This image was taken at an angle. Skin tone: FST V — 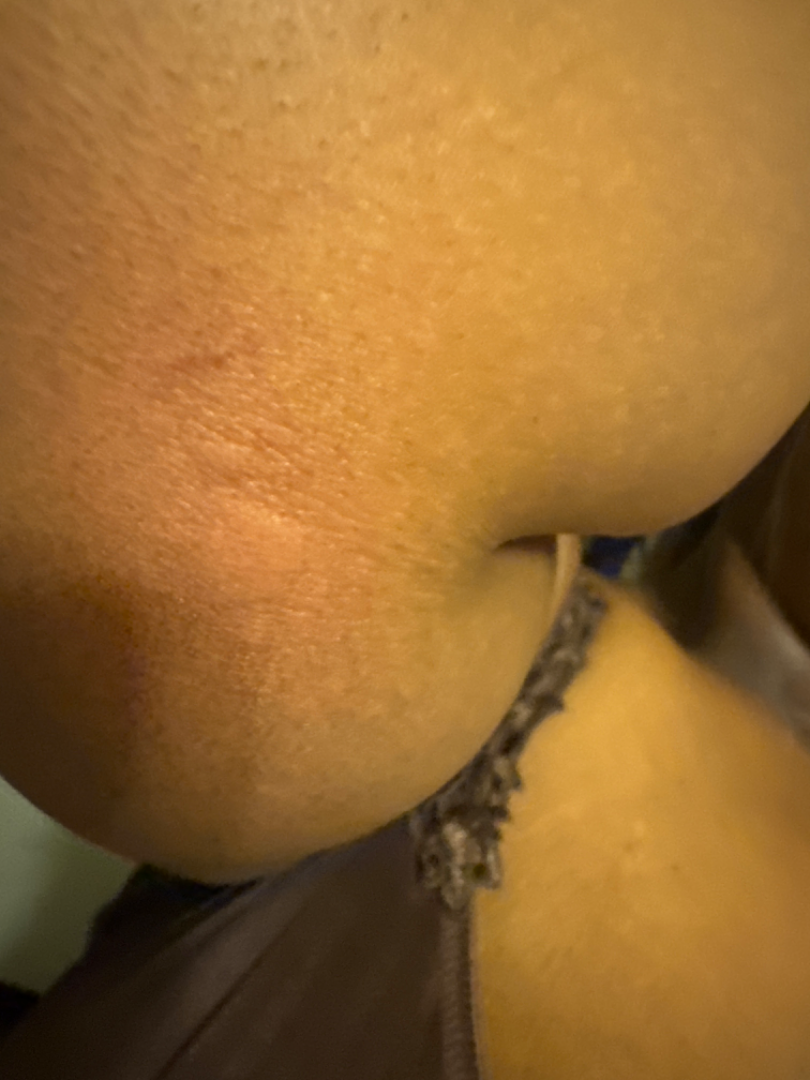Most likely Urticaria; also consider Allergic Contact Dermatitis.